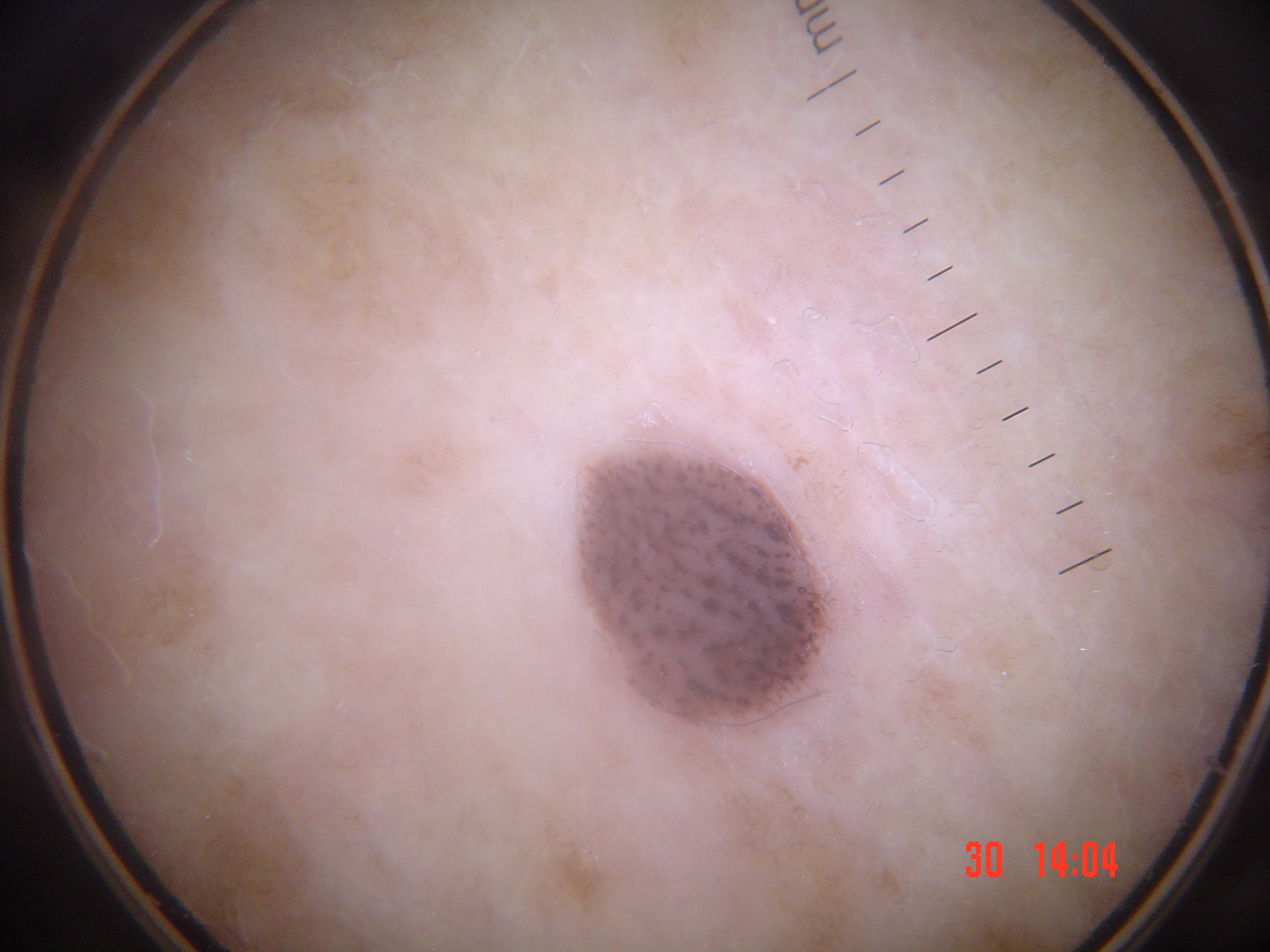The diagnosis was a benign, keratinocytic lesion — a seborrheic keratosis.